The subject is 30–39, female. This is a close-up image. The front of the torso, leg and back of the torso are involved — 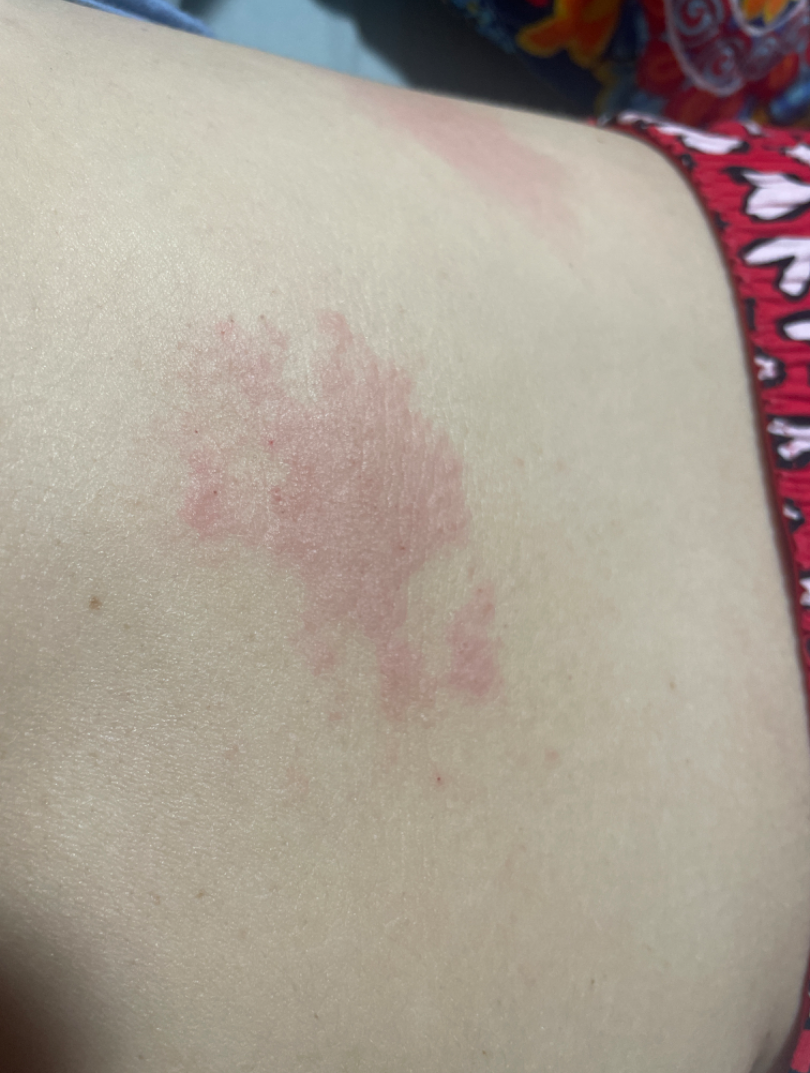The reviewing clinician's impression was: Herpes Zoster (primary); Acute dermatitis, NOS (considered).